A dermatoscopic image of a skin lesion.
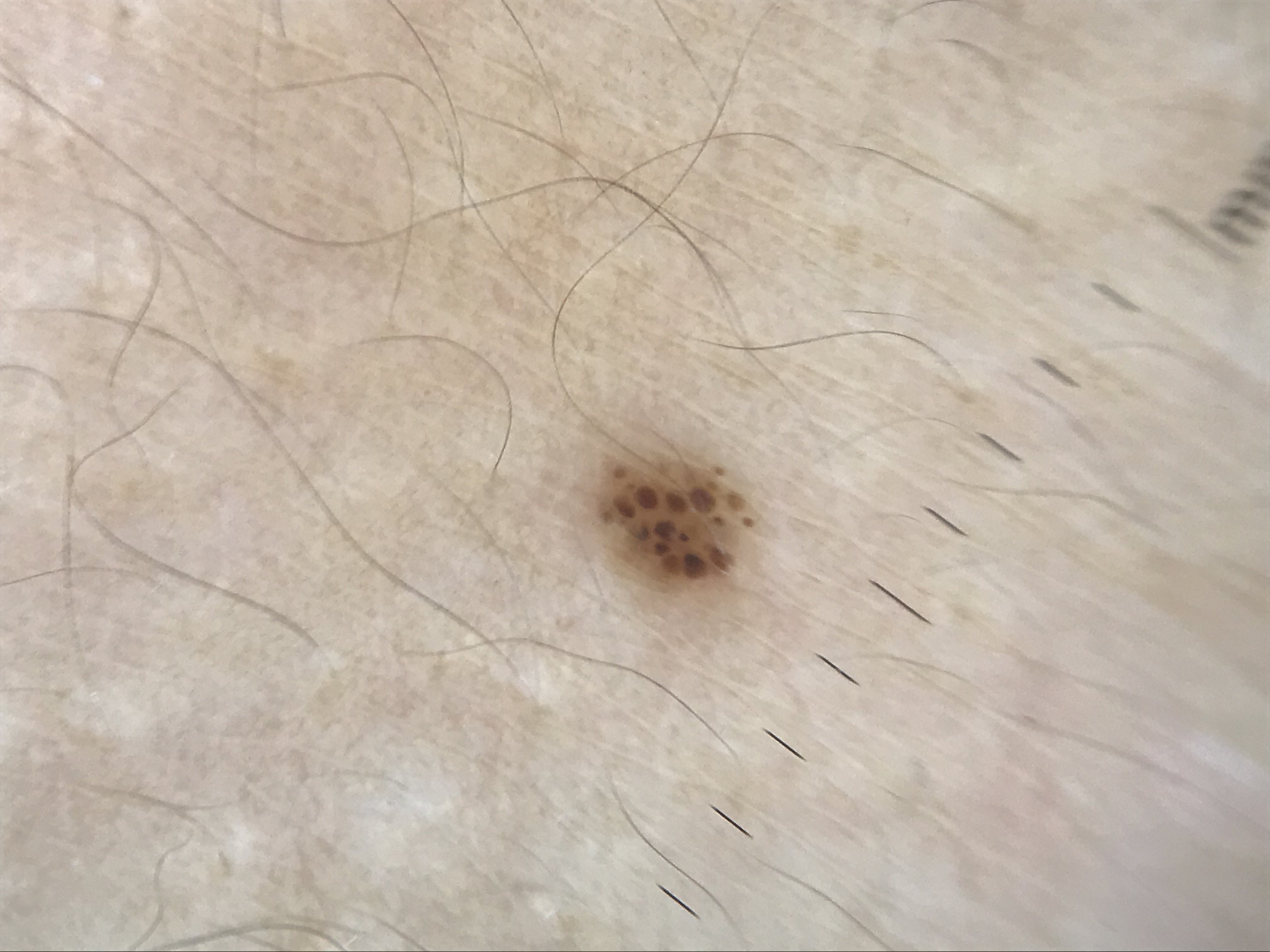lesion type — banal; diagnosis — junctional nevus (expert consensus).